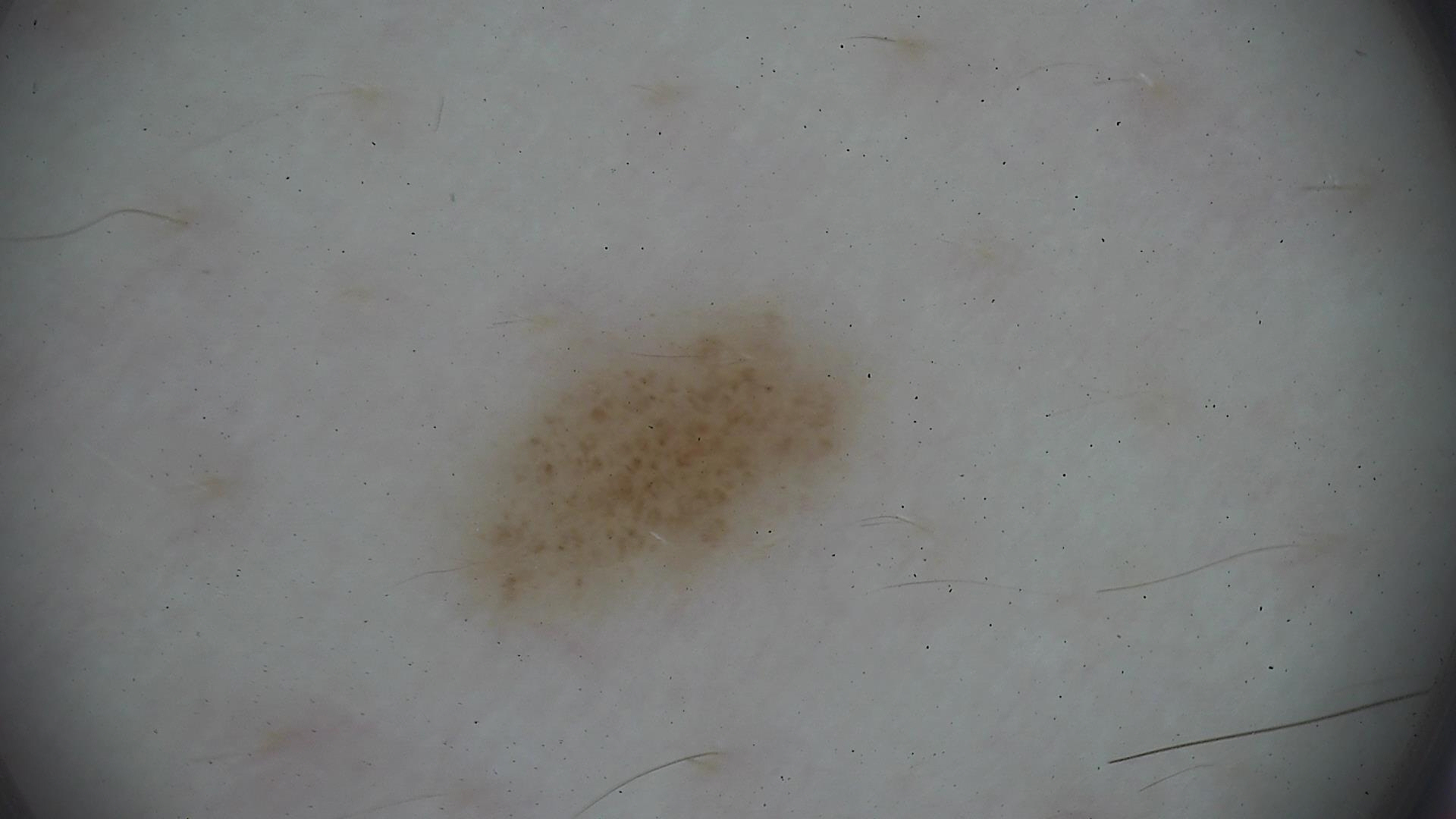A dermoscopic close-up of a skin lesion. Classified as a dysplastic junctional nevus.